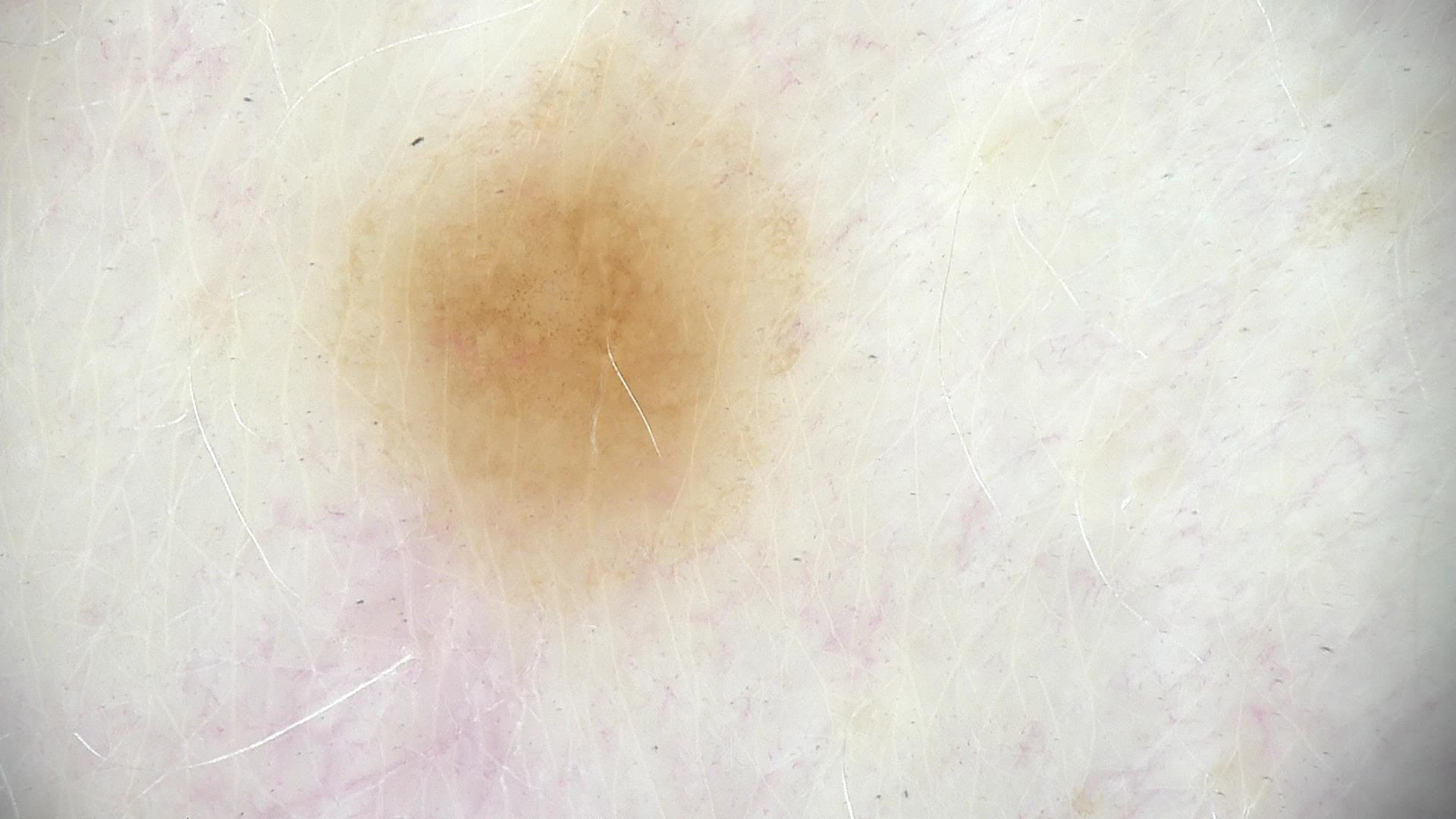Conclusion:
Consistent with a benign lesion — a dysplastic junctional nevus.